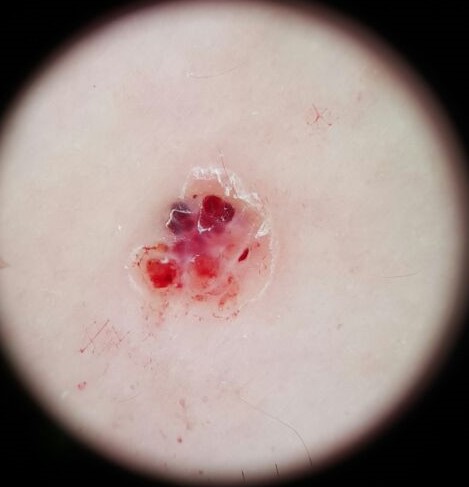Findings:
A skin lesion imaged with a dermatoscope. This is a vascular lesion.
Conclusion:
Labeled as an angiokeratoma.